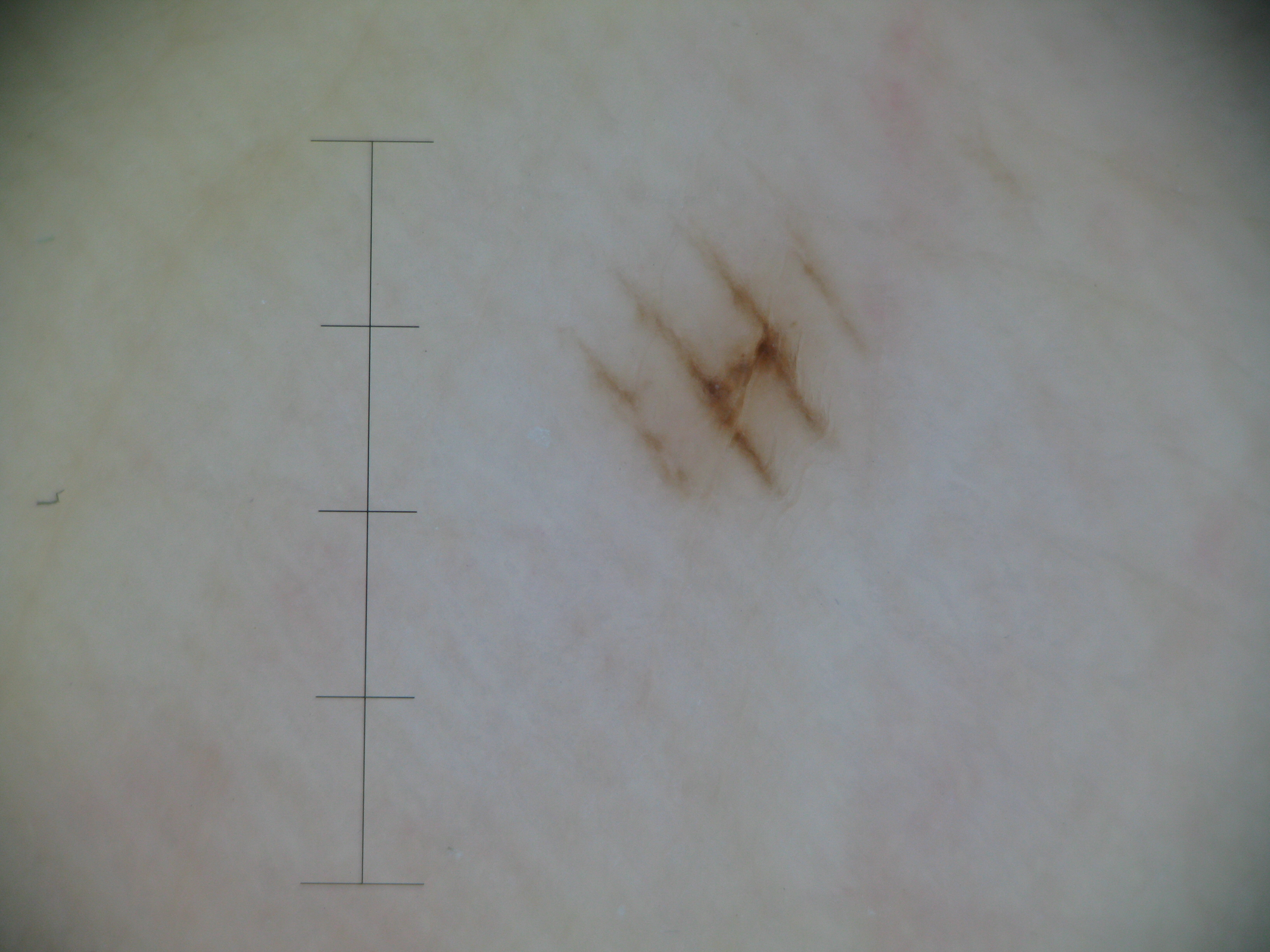Case:
– class · acral junctional nevus (expert consensus)